The patient is a female aged around 25, dermoscopy of a skin lesion:
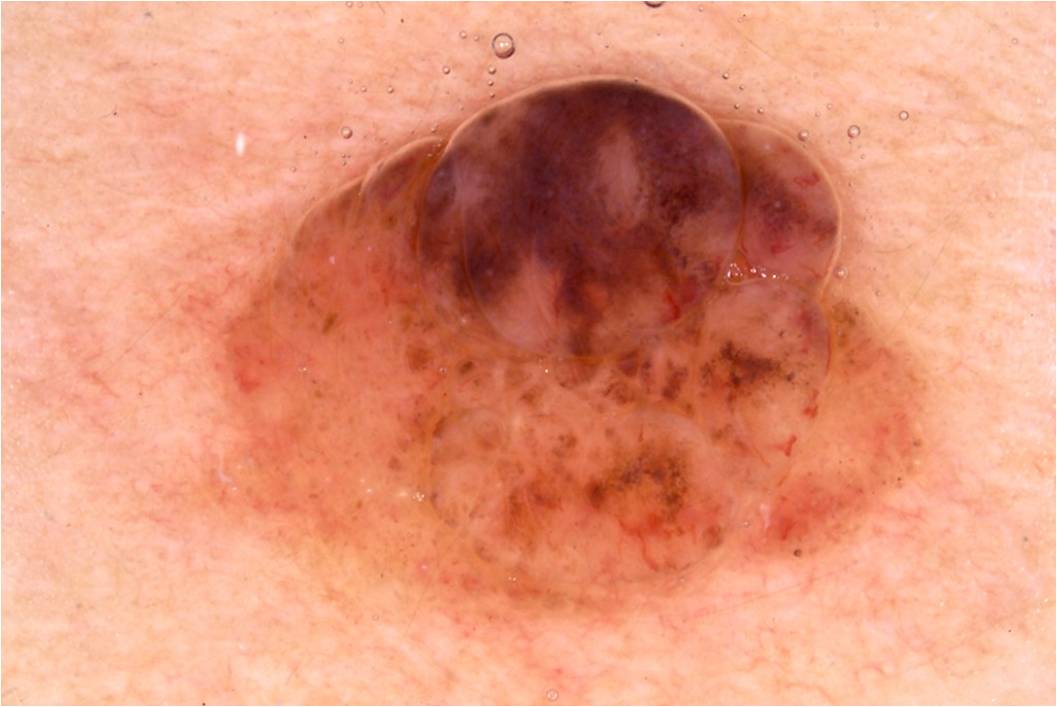Summary: A prominent lesion filling much of the field. On dermoscopy, the lesion shows pigment network. As (left, top, right, bottom), the lesion spans 201 73 938 626. Impression: The diagnostic assessment was a melanocytic nevus, a benign skin lesion.